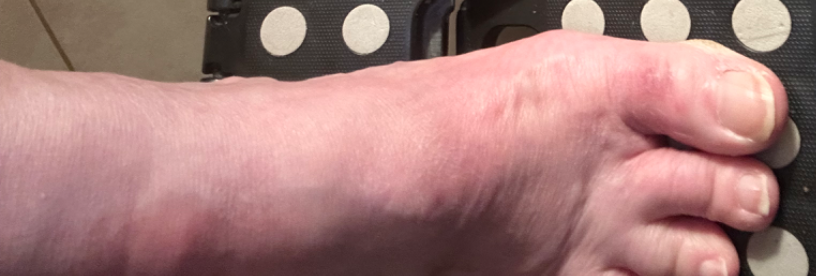The condition could not be reliably identified from the image. The patient reports burning, itching and enlargement. The patient is 70–79, female. An image taken at an angle. Present for less than one week. The patient reports the lesion is flat.